A dermatoscopic image of a skin lesion.
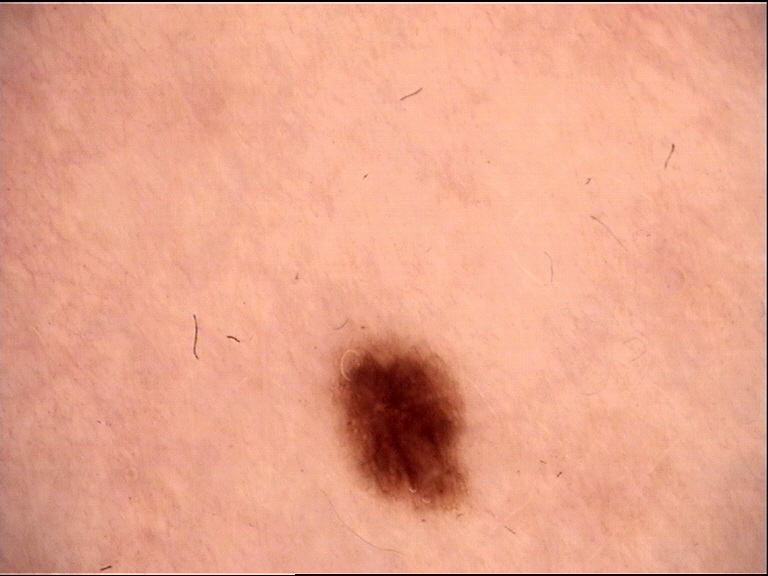Conclusion:
Labeled as a banal lesion — a junctional nevus.